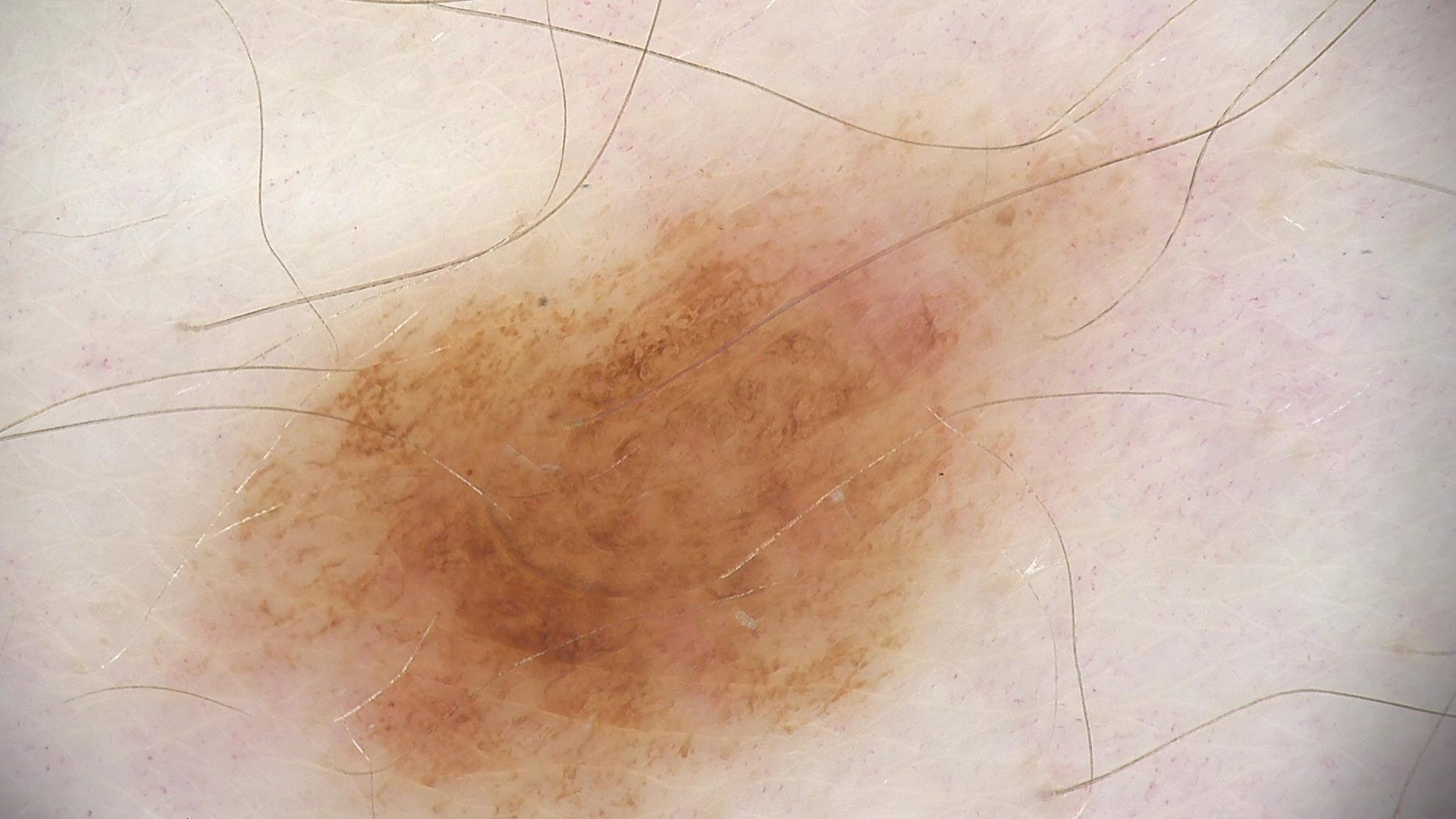image: dermoscopy | assessment: compound nevus (expert consensus).